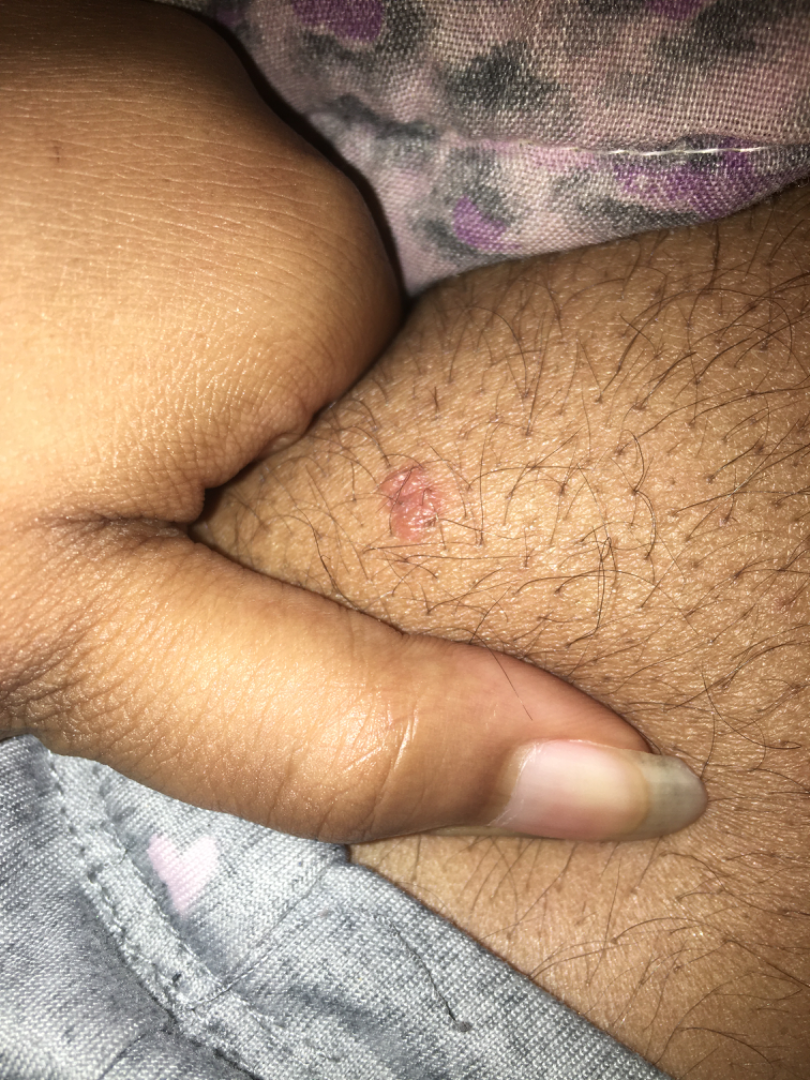{
  "patient": "female, age 18–29",
  "body_site": "leg",
  "shot_type": "close-up",
  "differential": {
    "tied_lead": [
      "Keratosis",
      "Verruca vulgaris",
      "Skin cancer"
    ]
  }
}